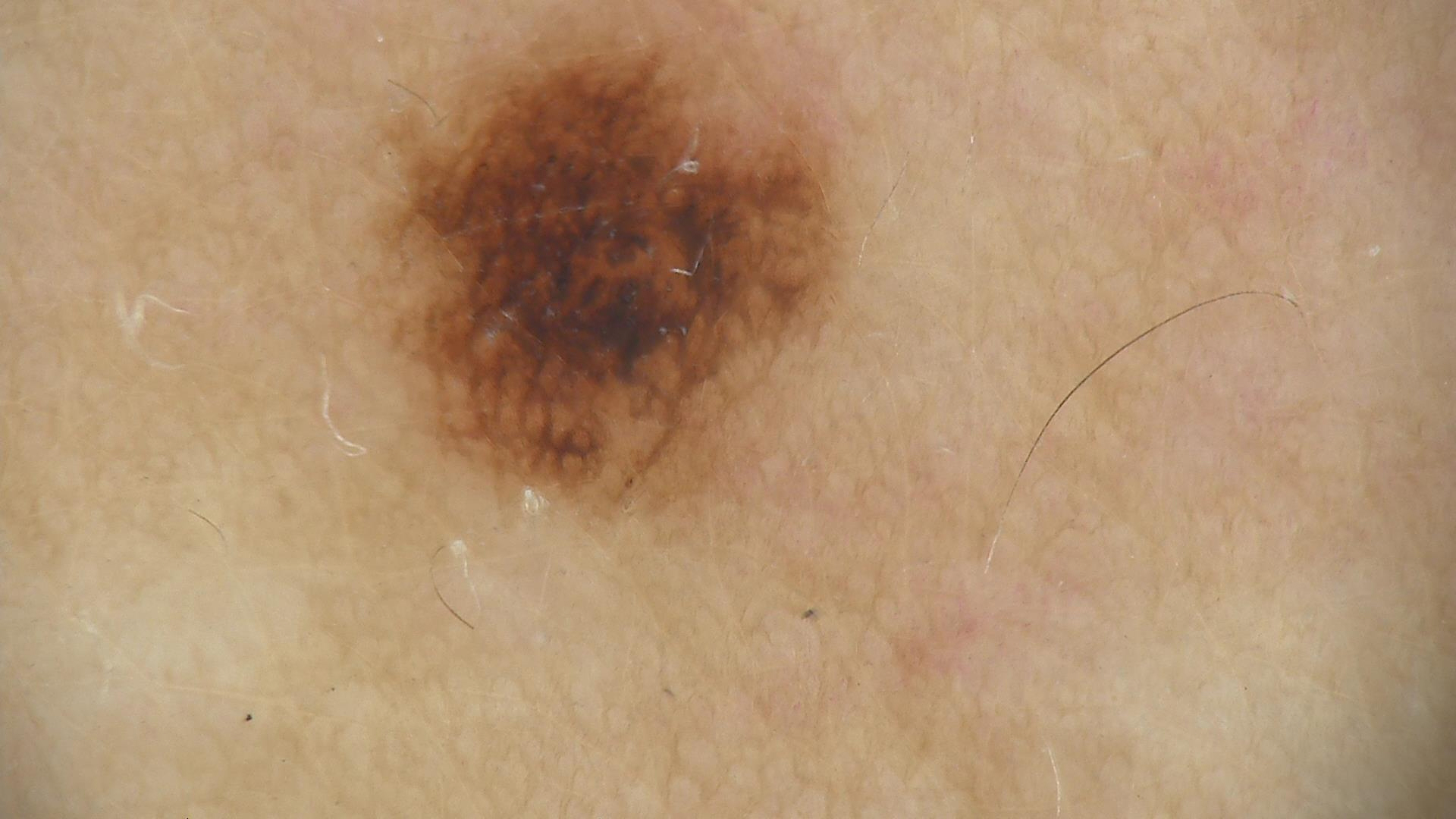{"diagnosis": {"name": "dysplastic junctional nevus", "code": "jd", "malignancy": "benign", "super_class": "melanocytic", "confirmation": "expert consensus"}}